This is a close-up image:
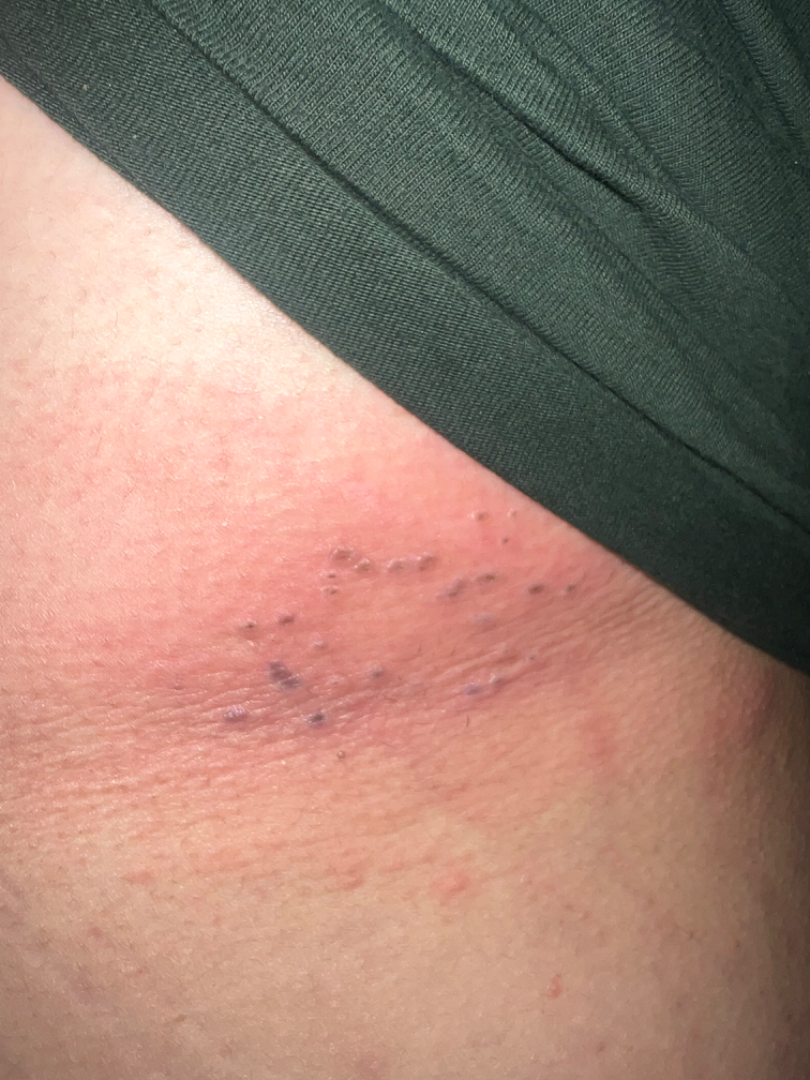Review:
Herpes Zoster (0.33); Allergic Contact Dermatitis (0.33); Herpes Simplex (0.33).